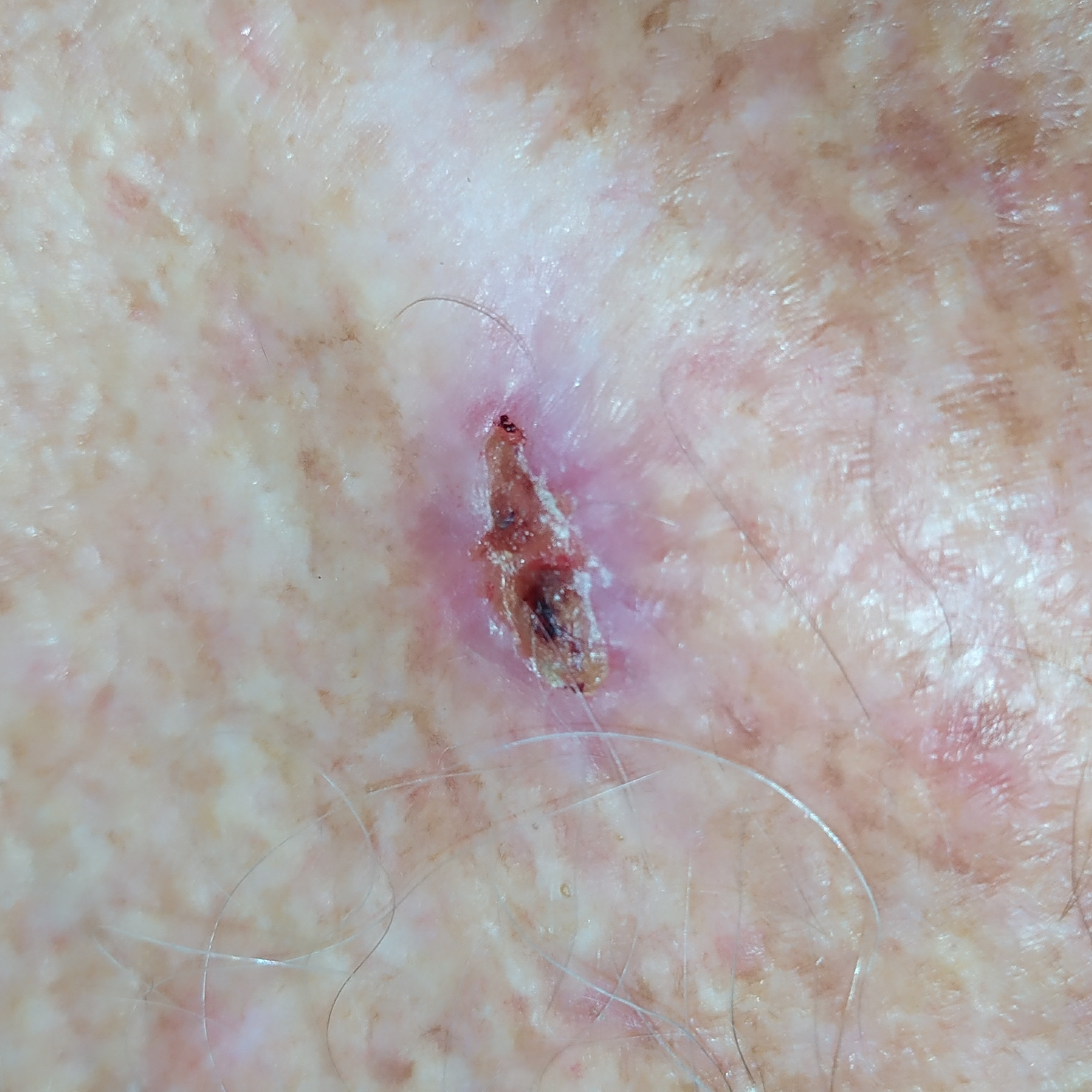The patient is Fitzpatrick II. A male subject 63 years of age. History notes prior malignancy (patient or family) and pesticide exposure. A clinical photograph showing a skin lesion. Measuring about 15 × 7 mm. Histopathological examination showed a malignancy — a basal cell carcinoma.